The patient reported no relevant symptoms from the lesion. No associated systemic symptoms reported. Female contributor, age 50–59. This is a close-up image. Present for one to four weeks.
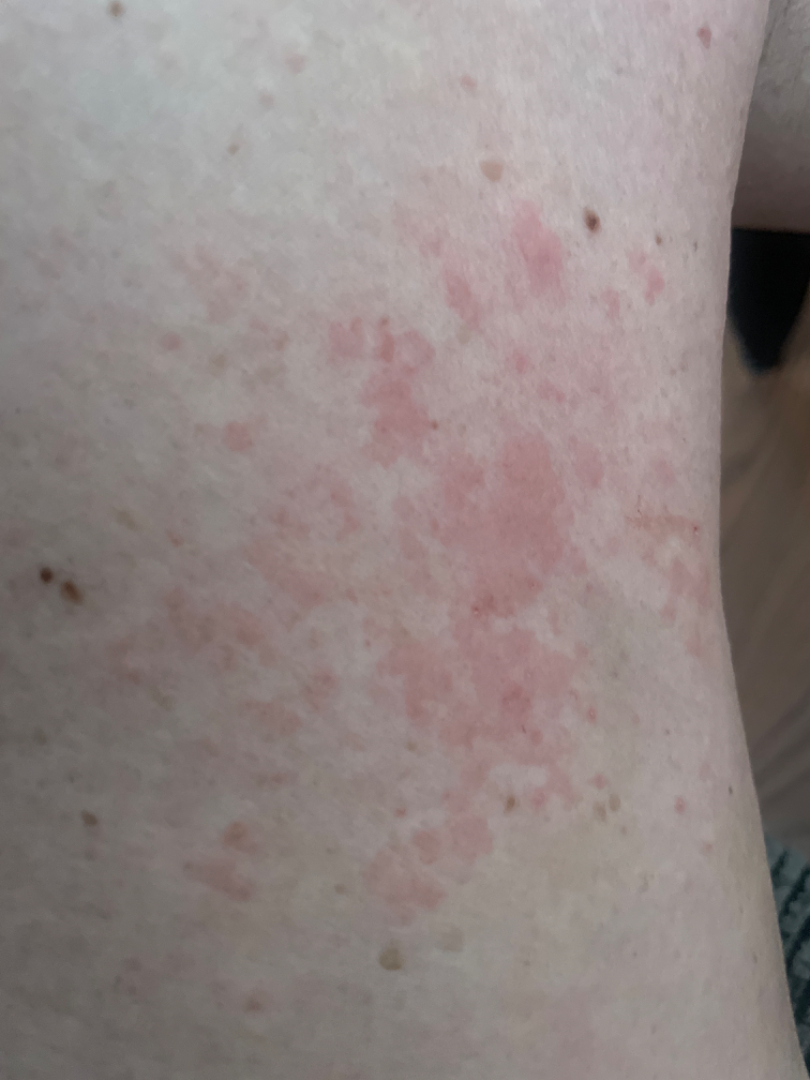Review:
Urticaria (primary).